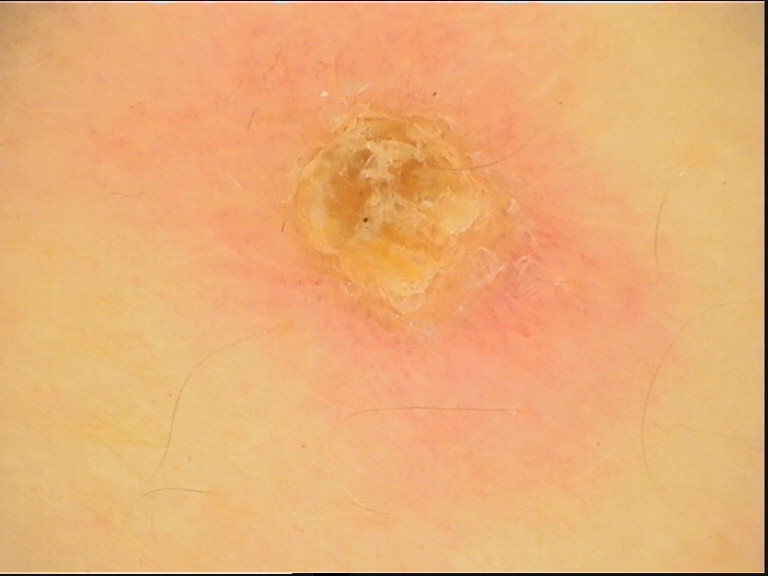image: dermoscopy
classification: keratinocytic
diagnosis: squamous cell carcinoma (biopsy-proven)